A dermoscopic photograph of a skin lesion:
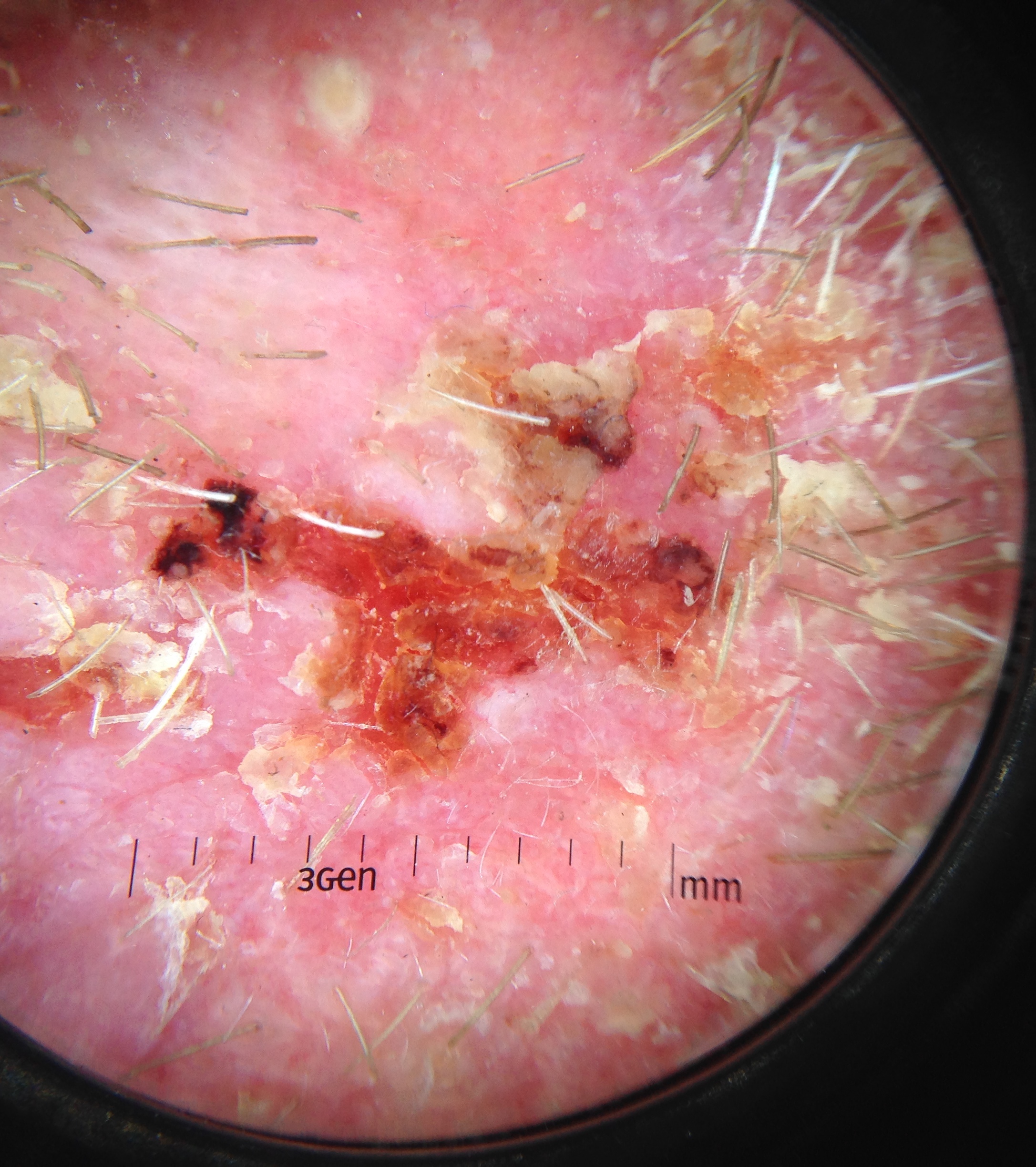lesion type: keratinocytic; label: squamous cell carcinoma (biopsy-proven).